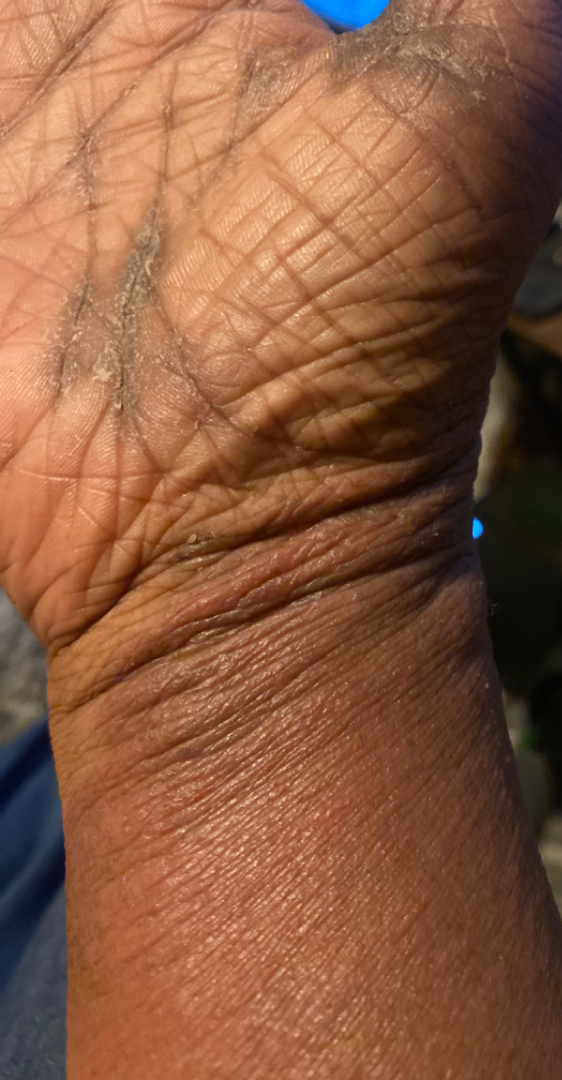The photo was captured at an angle. The affected area is the palm, back of the hand, arm and top or side of the foot. The subject is a female aged 40–49. Reviewed remotely by three dermatologists: consistent with Acute and chronic dermatitis.